Male contributor, age 40–49. This is a close-up image. The lesion involves the leg:
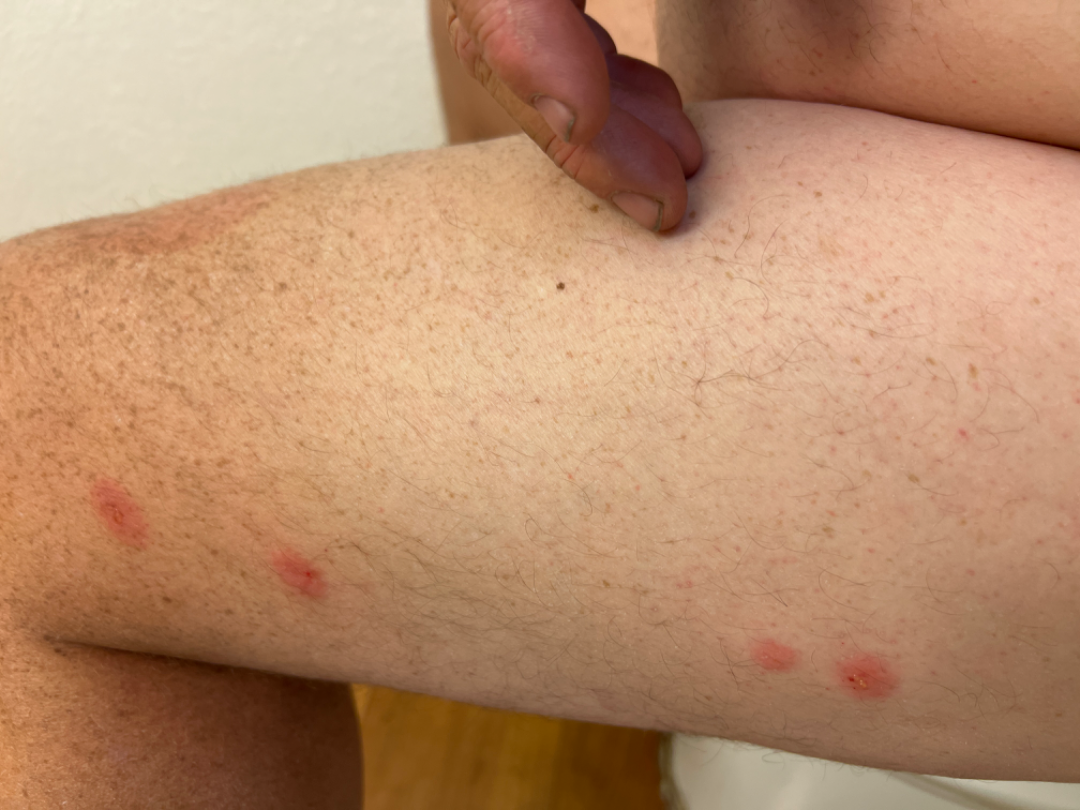The condition has been present for less than one week. Reported lesion symptoms include enlargement, itching and bothersome appearance. Texture is reported as raised or bumpy. Reviewed remotely by one dermatologist: the reviewer's impression was Eczema.